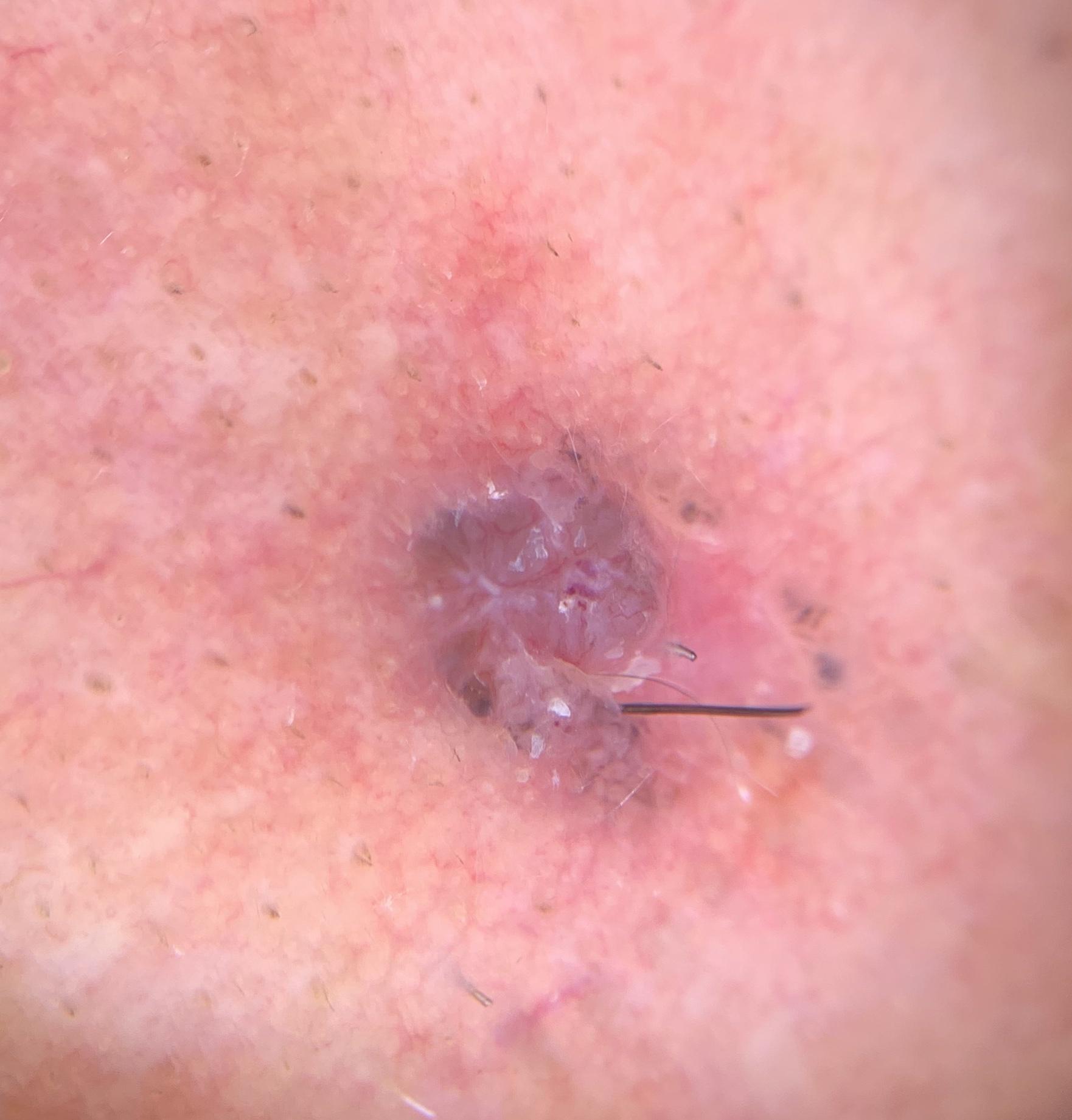<record>
  <patient>
    <age_approx>75</age_approx>
    <sex>male</sex>
  </patient>
  <image>contact-polarized dermoscopy</image>
  <skin_type>III</skin_type>
  <lesion_location>
    <region>the head or neck</region>
  </lesion_location>
  <diagnosis>
    <name>Basal cell carcinoma</name>
    <malignancy>malignant</malignancy>
    <confirmation>histopathology</confirmation>
    <lineage>adnexal</lineage>
  </diagnosis>
</record>